A dermoscopy image of a single skin lesion.
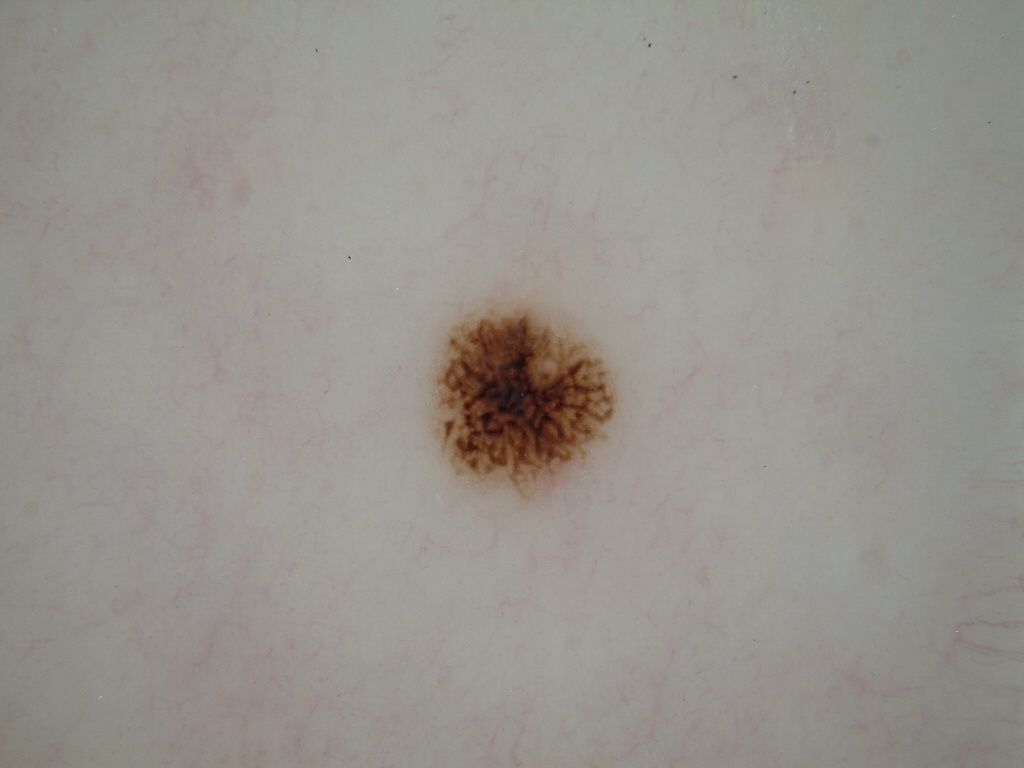Case summary:
* lesion bbox — 436/308/613/496
* dermoscopic pattern — pigment network; absent: negative network, streaks, milia-like cysts, and globules
* impression — a melanocytic nevus